Dermoscopy of a skin lesion.
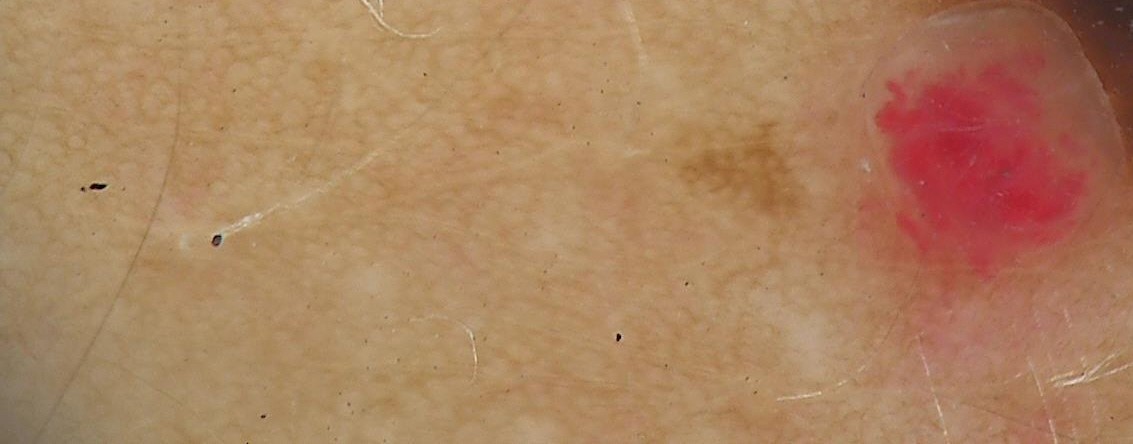Conclusion: The diagnosis was a benign lesion — a hemangioma.